A male subject in their mid- to late 30s; Fitzpatrick II.
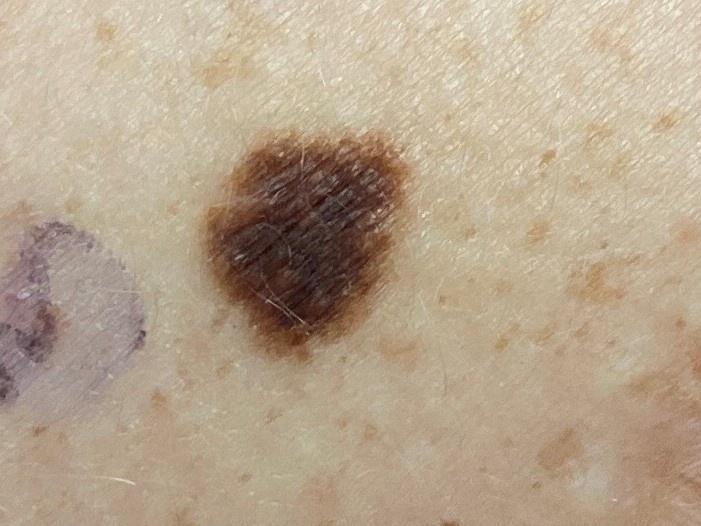Biopsy-confirmed as a benign lesion — a nevus.